A dermatoscopic image of a skin lesion.
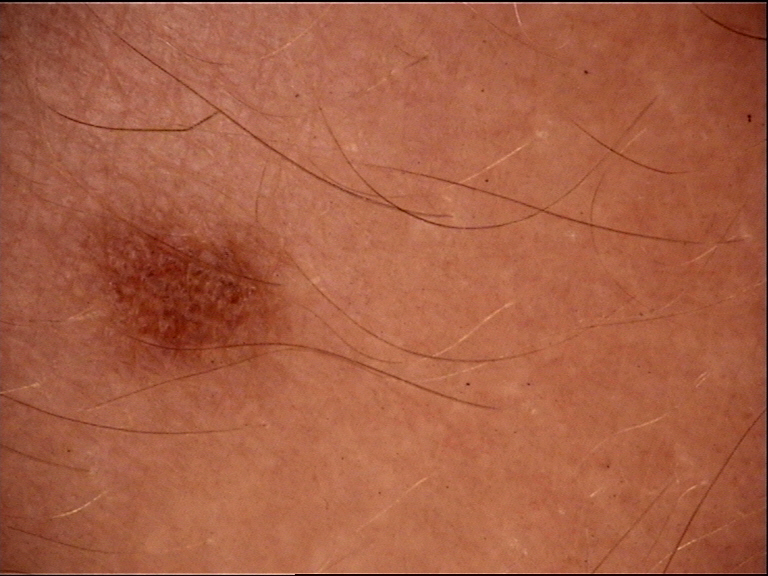Classified as a banal lesion — a junctional nevus.